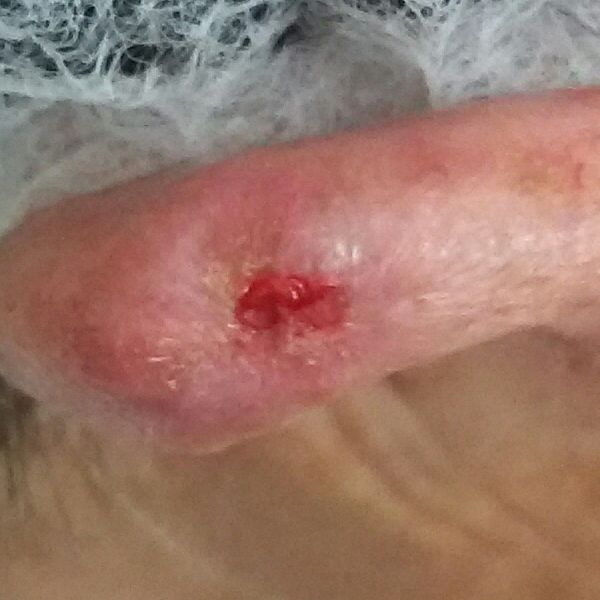- image type · clinical photograph
- patient · female, aged 67
- FST · III
- body site · an ear
- lesion diameter · 13x8 mm
- patient-reported symptoms · elevation, itching, pain, growth, bleeding
- pathology · squamous cell carcinoma (biopsy-proven)